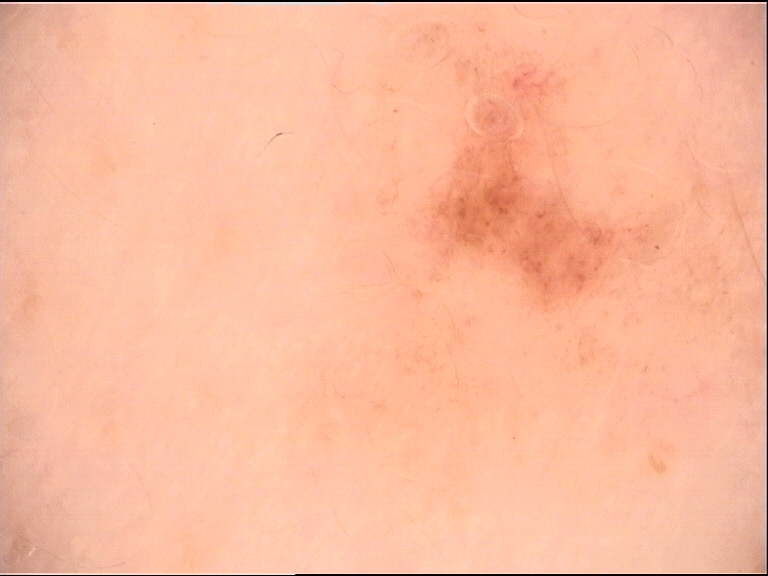The diagnostic label was a dysplastic junctional nevus.